The patient is a female aged 40–49. The lesion is associated with itching, enlargement and burning. An image taken at a distance. The contributor notes the lesion is raised or bumpy and rough or flaky. The front of the torso and head or neck are involved. Present for less than one week. The contributor notes associated shortness of breath and fatigue:
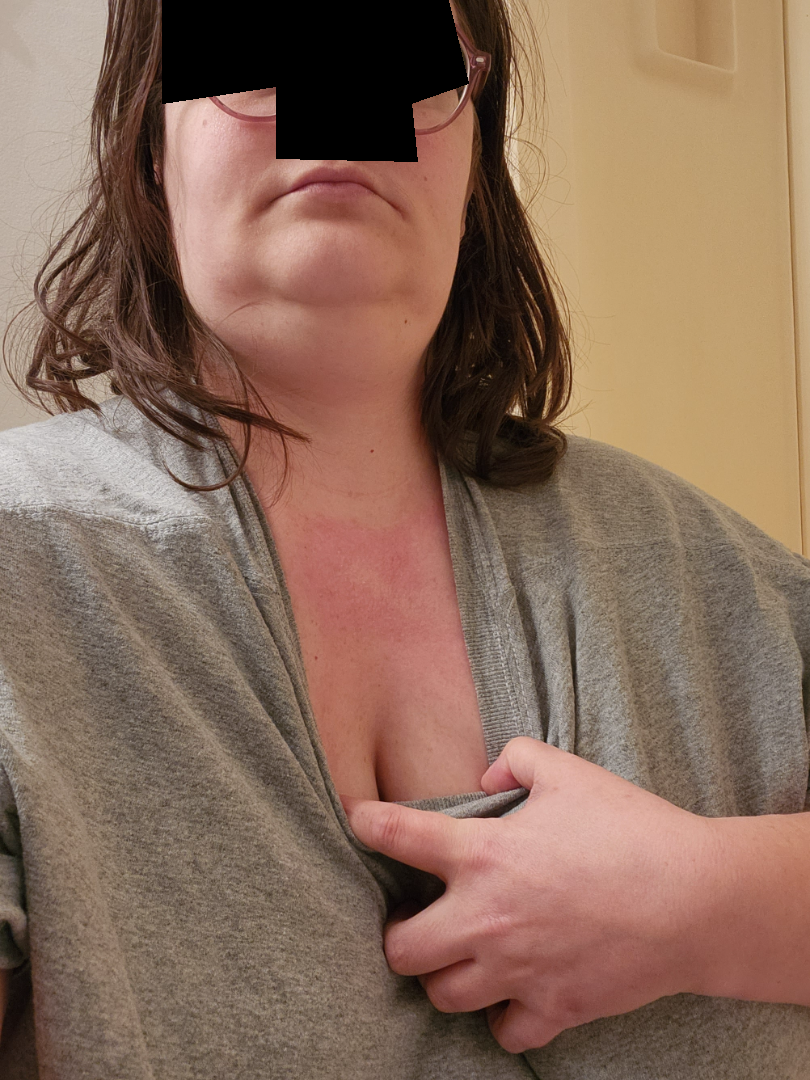On independent review by the dermatologists, most consistent with Allergic Contact Dermatitis; also on the differential is Photodermatitis; a remote consideration is Drug Rash; less likely is Acute dermatitis, NOS; less probable is Rosacea.